Reported lesion symptoms include bothersome appearance and itching; texture is reported as raised or bumpy; the back of the hand and front of the torso are involved; present for less than one week; the contributor is 30–39, female; the photo was captured at a distance — 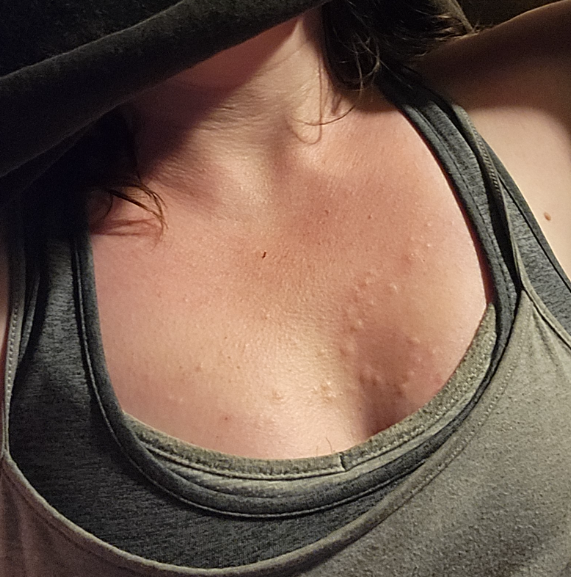assessment: could not be assessed